A clinical photograph of a skin lesion; a patient in their 30s.
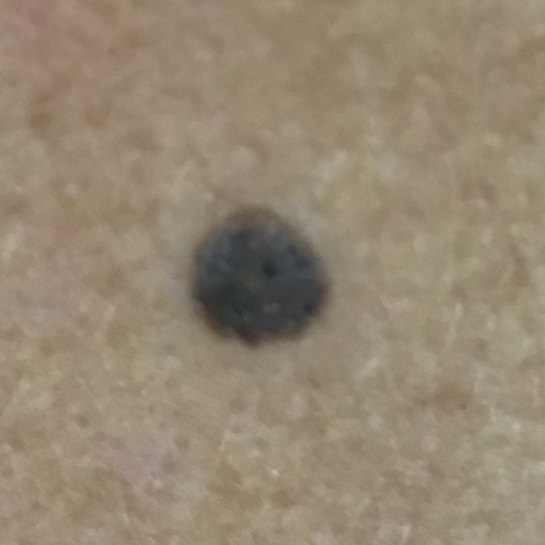The lesion was found on an arm. The patient reports that the lesion is elevated, but does not hurt. Diagnosed by dermatologist consensus as a nevus.